A dermoscopic view of a skin lesion, the patient is a female aged 43-47.
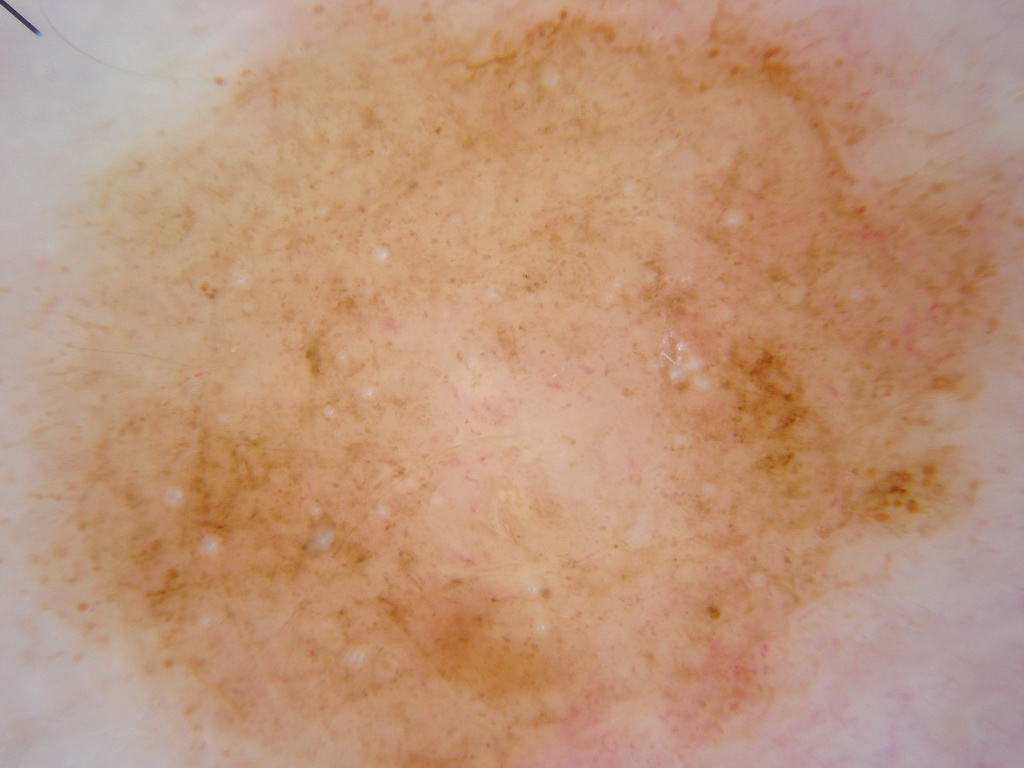{
  "lesion_location": "spans the dermoscopic field",
  "dermoscopic_features": {
    "present": [
      "globules",
      "pigment network"
    ],
    "absent": [
      "milia-like cysts",
      "negative network",
      "streaks"
    ]
  },
  "diagnosis": {
    "name": "melanocytic nevus",
    "malignancy": "benign",
    "lineage": "melanocytic",
    "provenance": "clinical"
  }
}